A skin lesion imaged with a dermatoscope · the subject is a female aged 63-67.
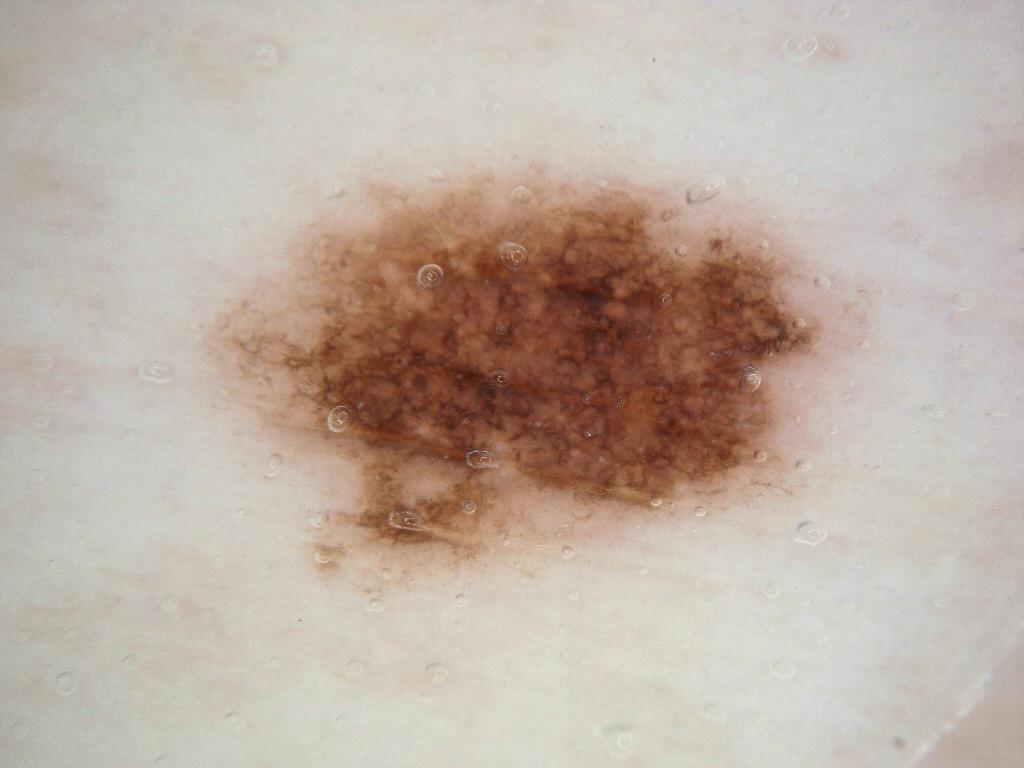On dermoscopy, the lesion shows pigment network. The lesion's extent is x1=201 y1=165 x2=865 y2=589. The diagnostic assessment was a melanocytic nevus, a benign skin lesion.